This is a close-up image · the affected area is the leg · the subject is a male aged 60–69.
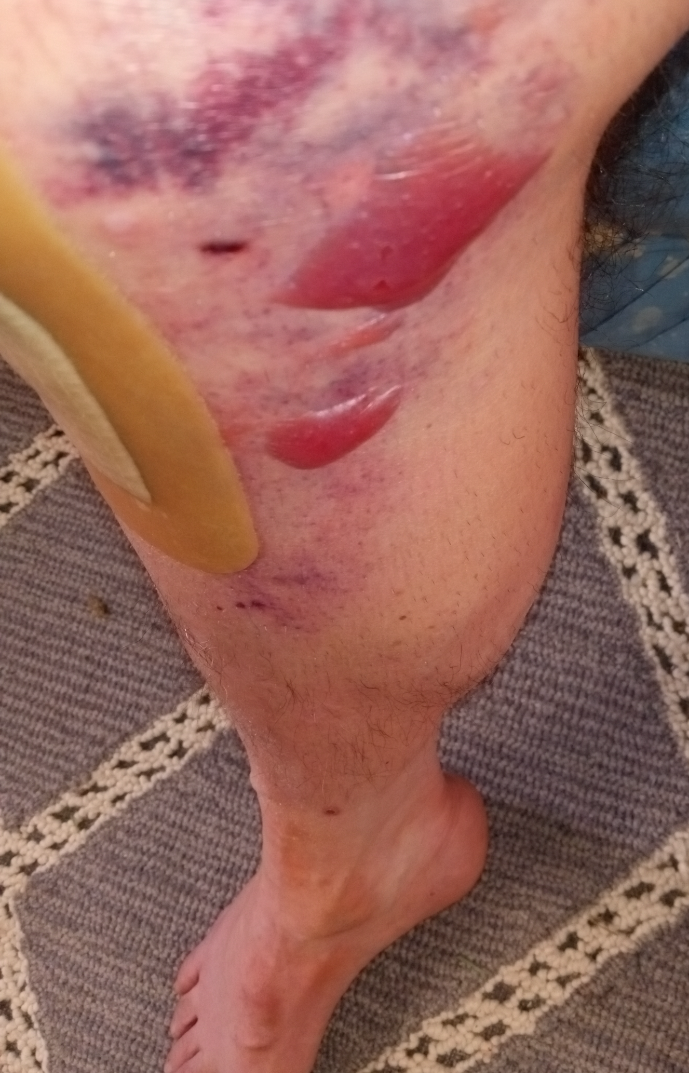<report>
  <assessment>indeterminate from the photograph</assessment>
  <texture>fluid-filled</texture>
  <systemic_symptoms>joint pain</systemic_symptoms>
  <symptoms>enlargement</symptoms>
  <duration>less than one week</duration>
  <patient_category>skin that appeared healthy to them</patient_category>
</report>